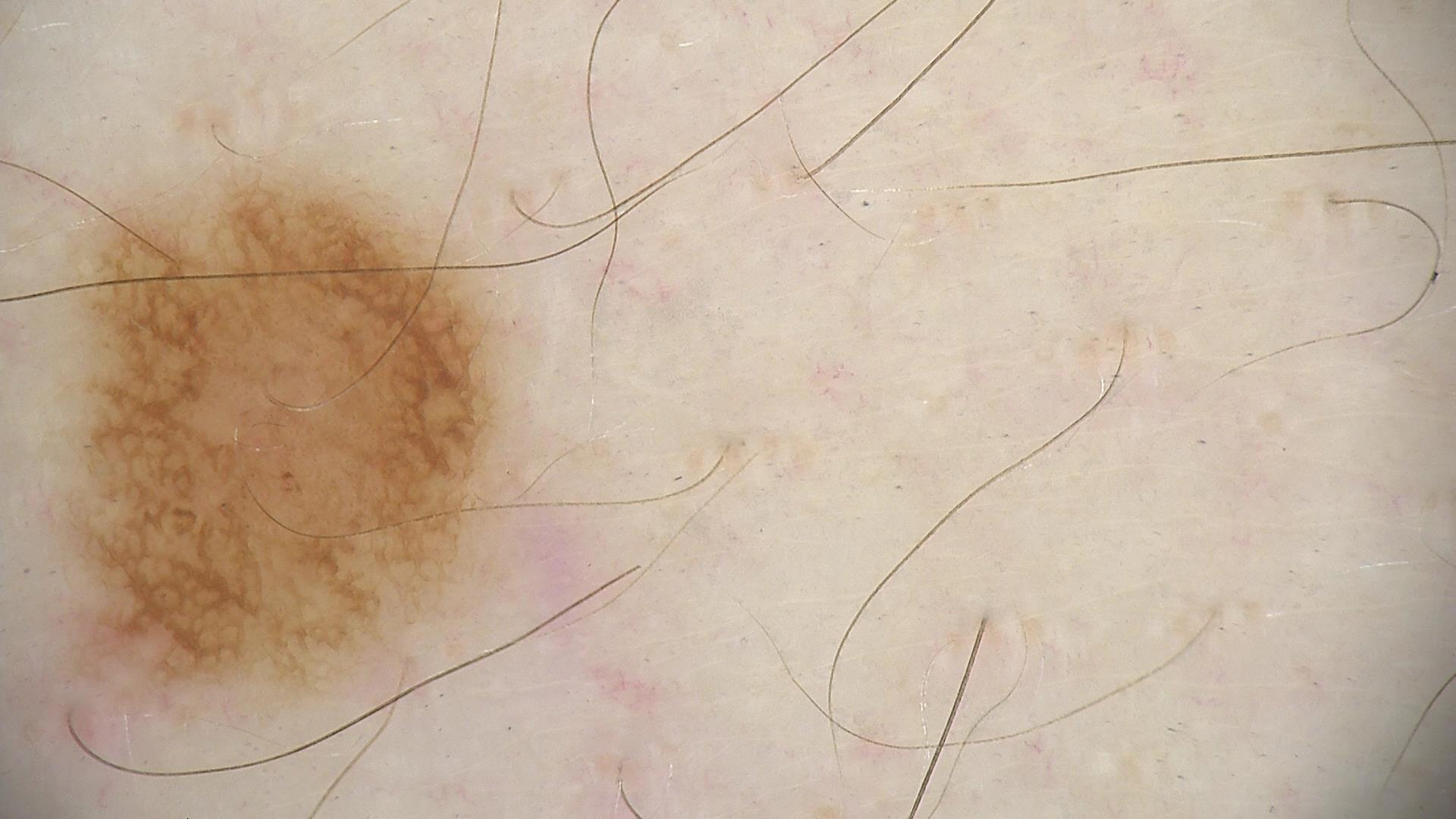modality: dermatoscopy
diagnosis: dysplastic junctional nevus (expert consensus)